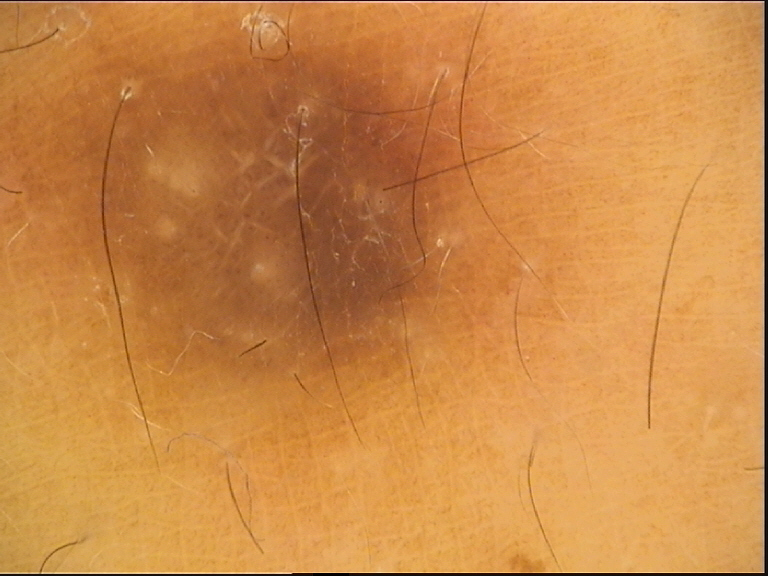{"lesion_type": {"main_class": "fibro-histiocytic"}, "diagnosis": {"name": "dermatofibroma", "code": "df", "malignancy": "benign", "super_class": "non-melanocytic", "confirmation": "expert consensus"}}